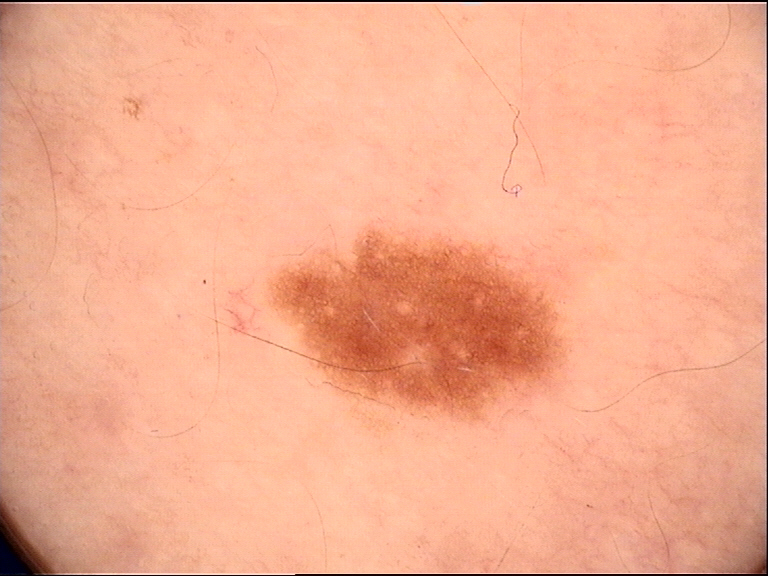Case:
- label · dysplastic junctional nevus (expert consensus)